The affected area is the arm · close-up view — 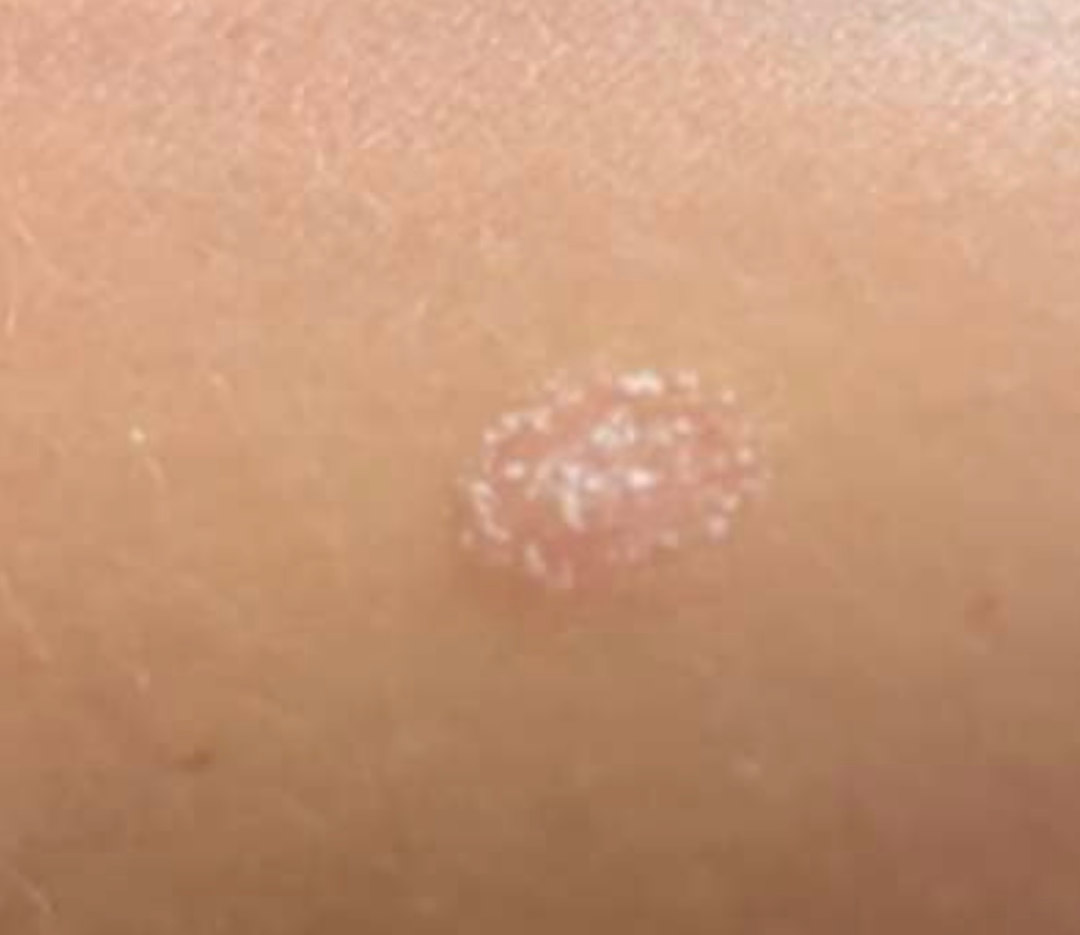Q: What is the dermatologist's impression?
A: the differential is split between Psoriasis and Eczema; a remote consideration is Pityriasis rosea